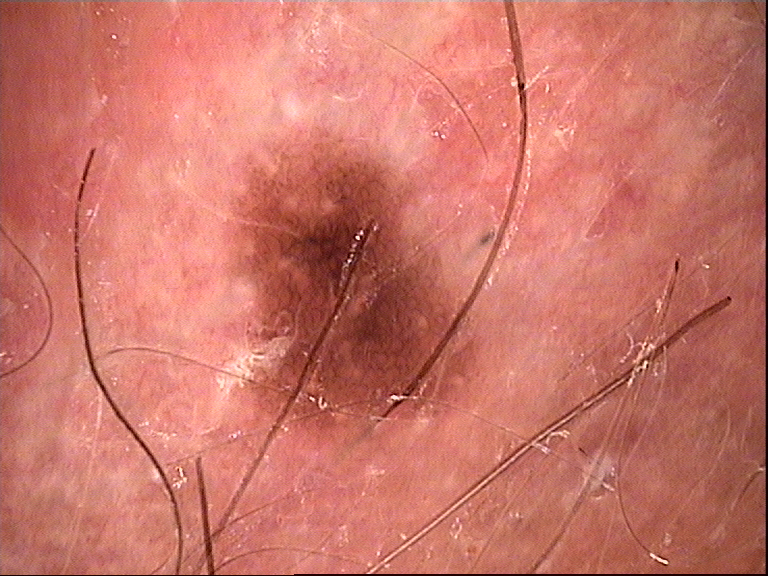Q: What is the diagnosis?
A: dysplastic junctional nevus (expert consensus)